The subject is a male aged 63 to 67. A dermoscopic close-up of a skin lesion.
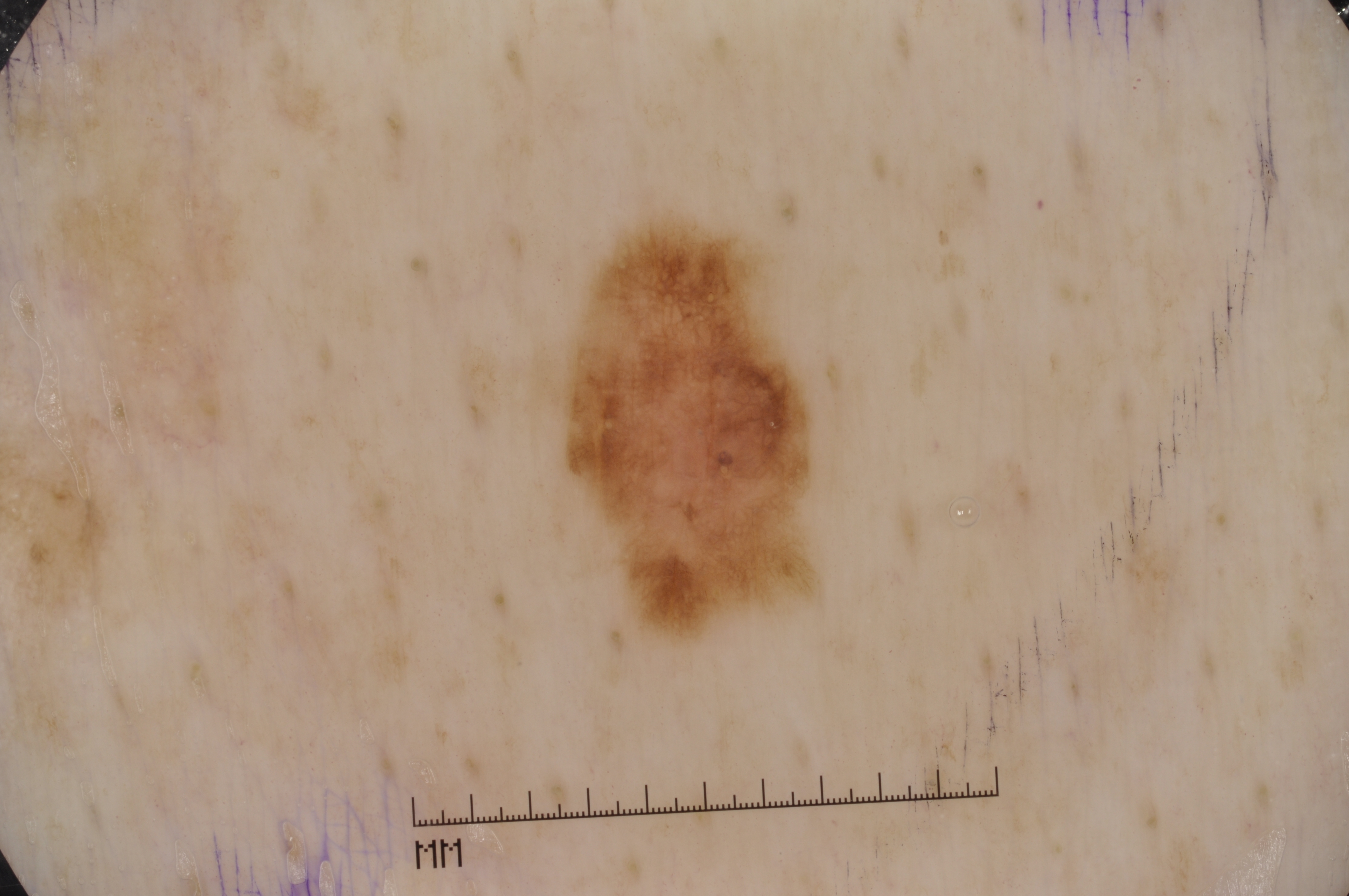dermoscopic pattern — pigment network | location — [559,224,811,637] | diagnosis — a melanocytic nevus.